A dermoscopic image of a skin lesion.
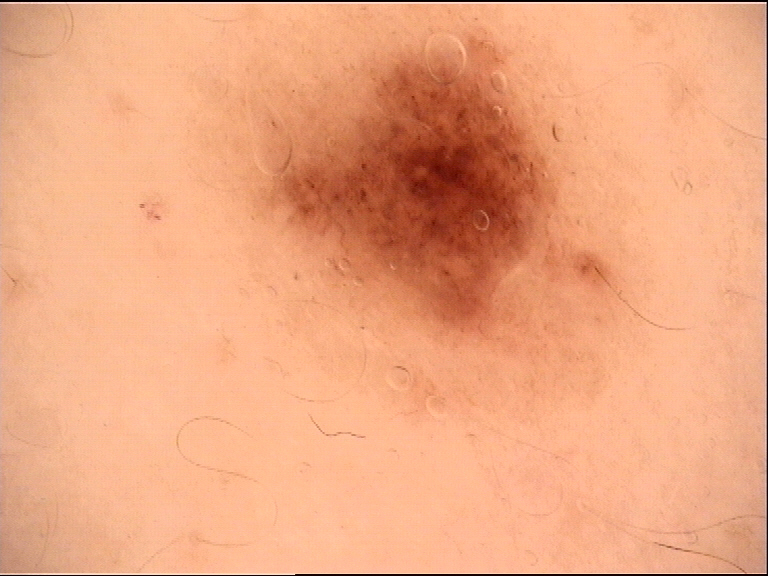Labeled as a benign lesion — a dysplastic junctional nevus.